Close-up view; male patient, age 18–29; located on the top or side of the foot, arm, front of the torso, leg and back of the hand — 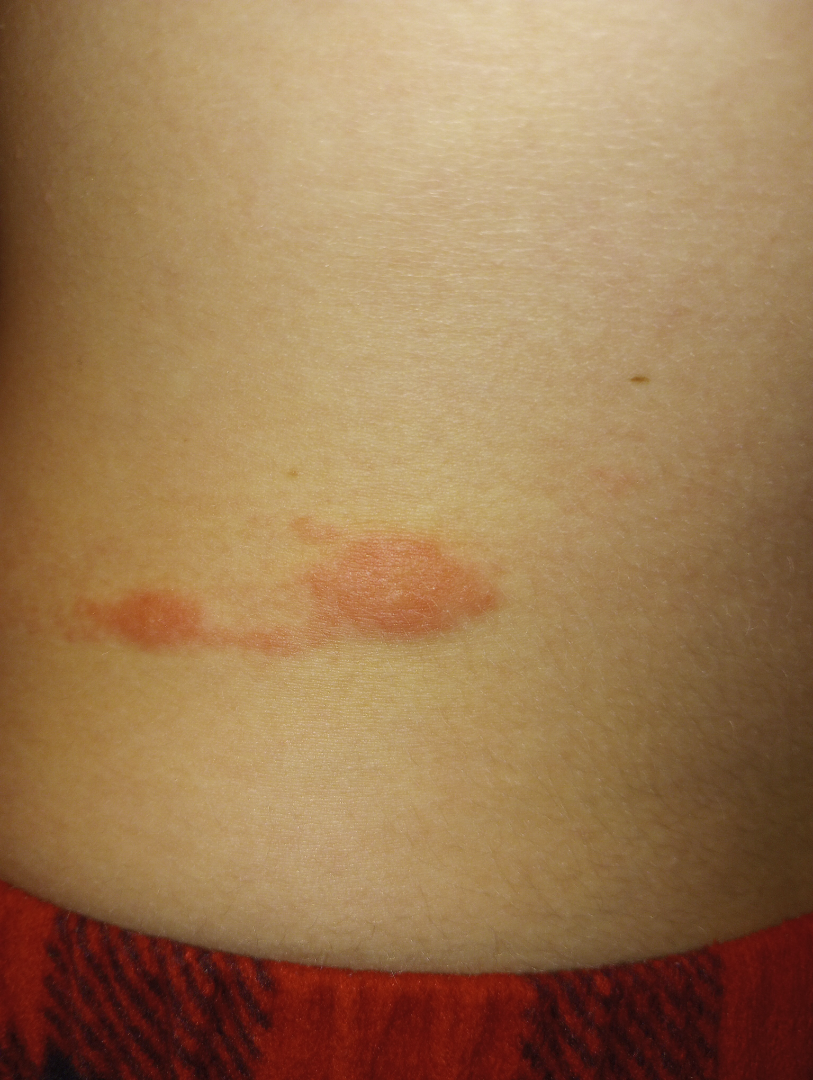differential:
  tied_lead:
    - Allergic Contact Dermatitis
    - Irritant Contact Dermatitis